The leg is involved. The photograph was taken at a distance:
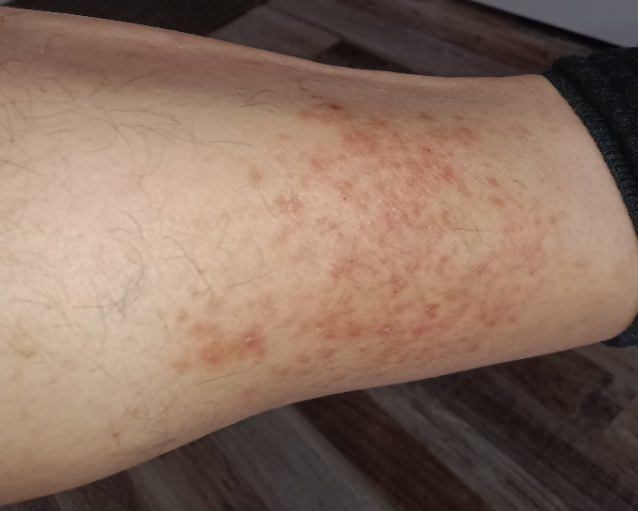| field | value |
|---|---|
| surface texture | raised or bumpy |
| assessment | most consistent with Eczema |